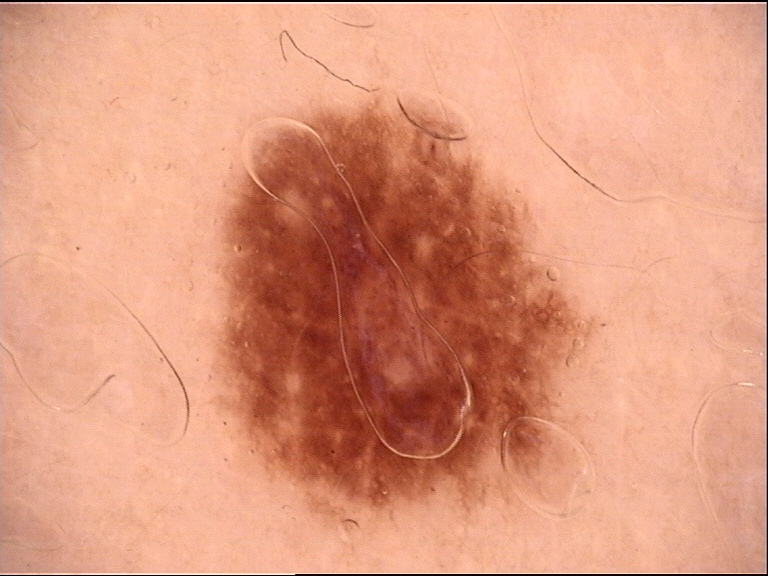  diagnosis:
    name: dysplastic junctional nevus
    code: jd
    malignancy: benign
    super_class: melanocytic
    confirmation: expert consensus